Referred for assessment of suspected basal cell carcinoma; the patient reports a personal history of cancer and a family history of skin cancer; the patient says their skin tans without first burning; a dermoscopic image of a skin lesion; a female subject age 92: 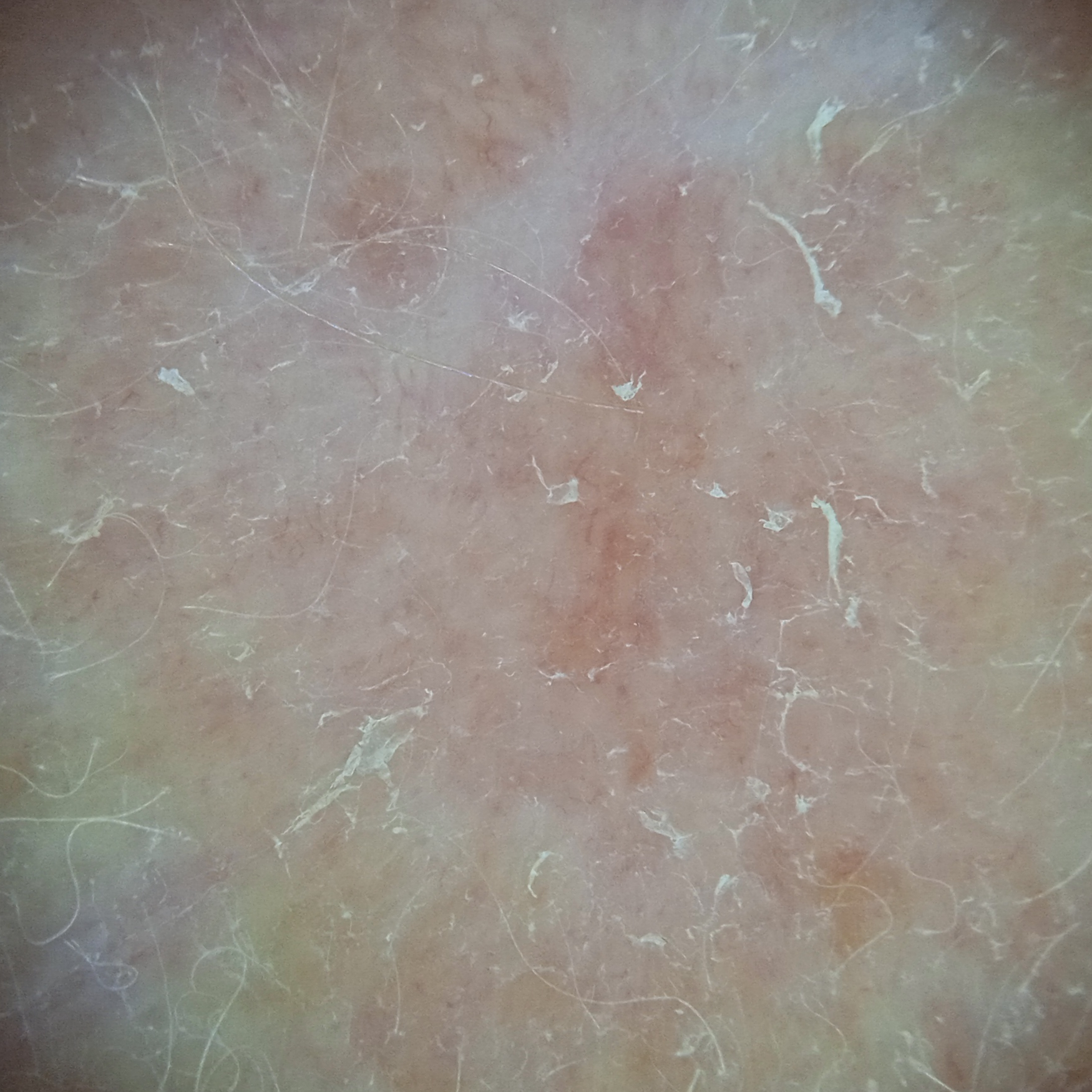The lesion is about 11.5 mm across.
On biopsy, the diagnosis was a basal cell carcinoma, following excision, with tumor thickness 2.6 mm.